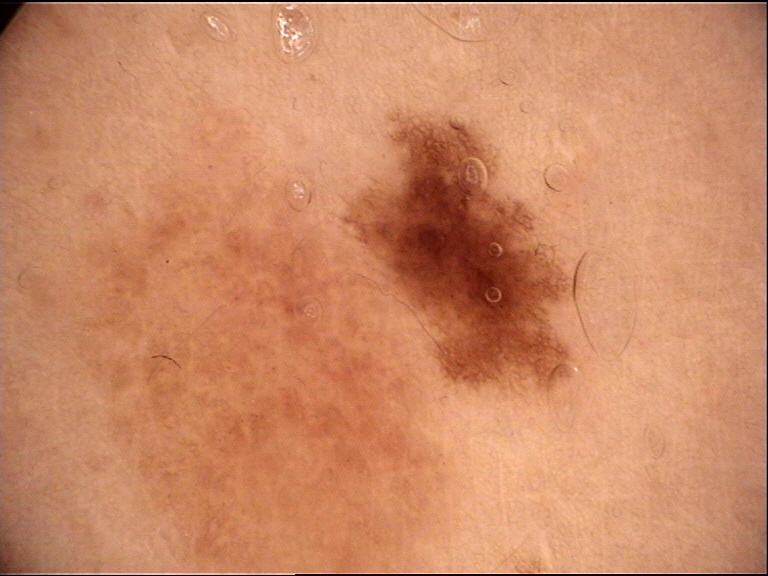  diagnosis:
    name: dysplastic junctional nevus
    code: jd
    malignancy: benign
    super_class: melanocytic
    confirmation: expert consensus